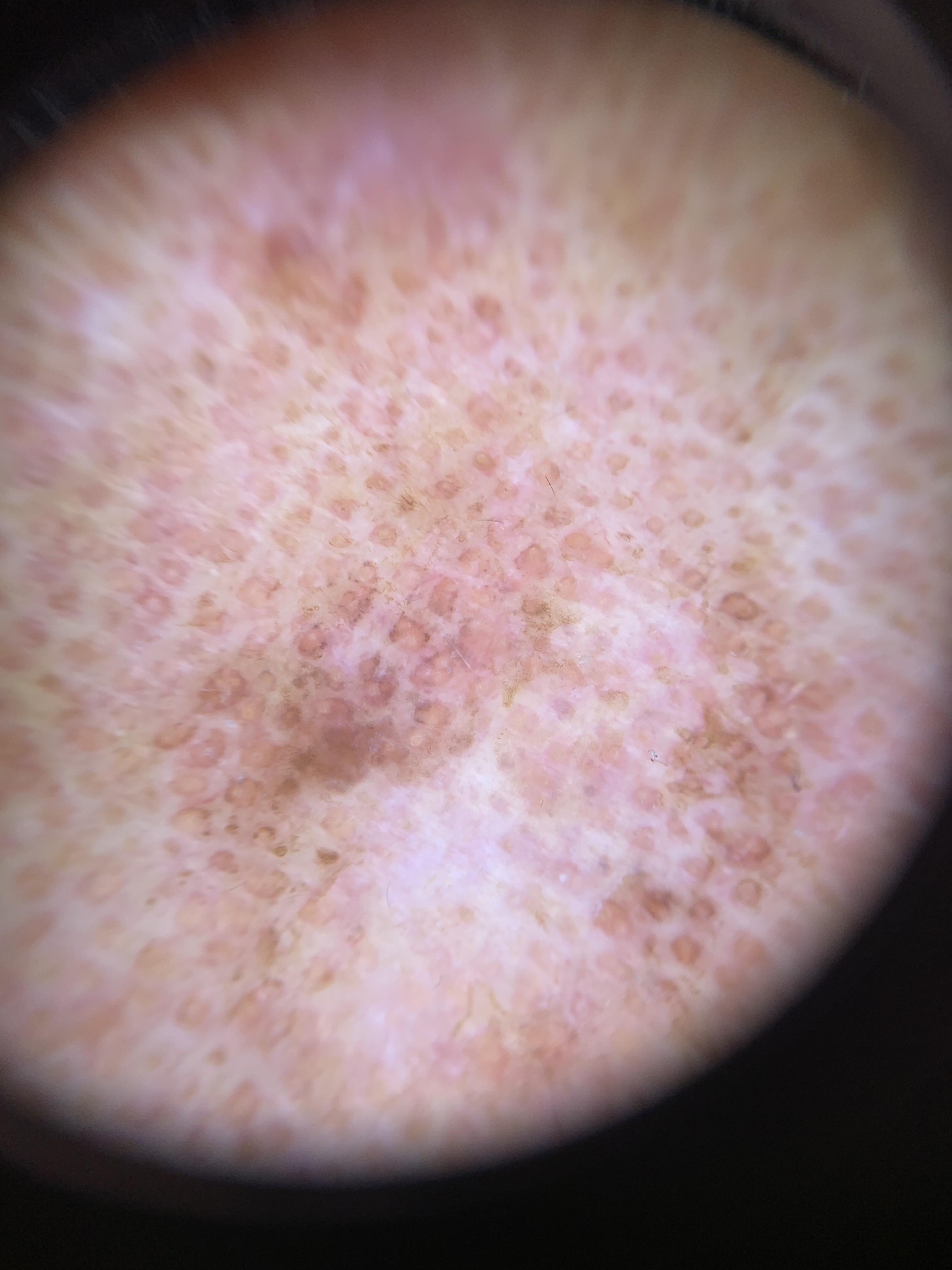subject=male, aged 73 to 77; imaging=dermoscopy; anatomic site=the head or neck; diagnostic label=Solar or actinic keratosis (clinical impression).